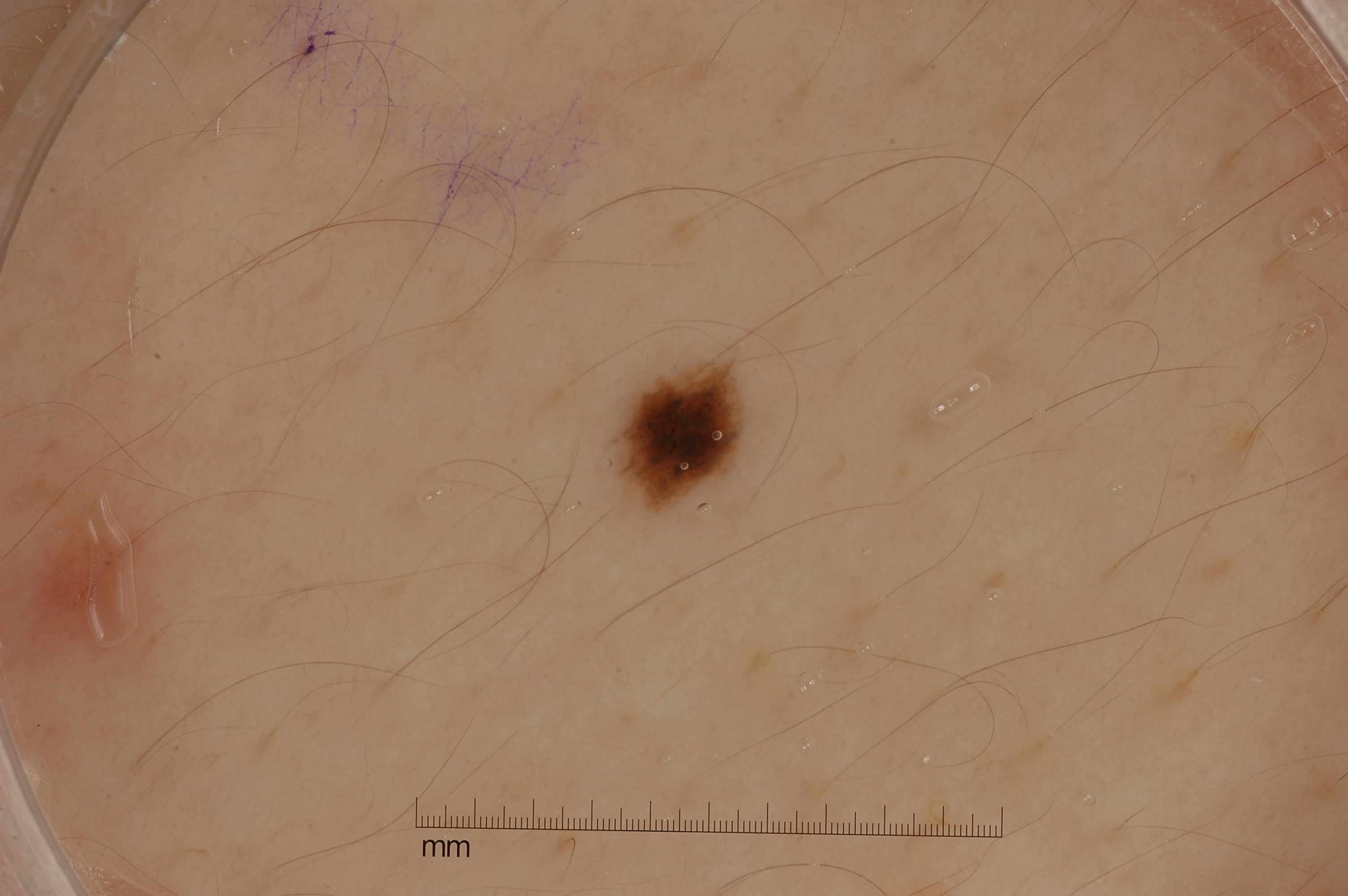A dermoscopy image of a single skin lesion.
As (left, top, right, bottom), lesion location: 608/358/748/512.
The clinical diagnosis was a melanocytic nevus.